A female patient 46 years old: 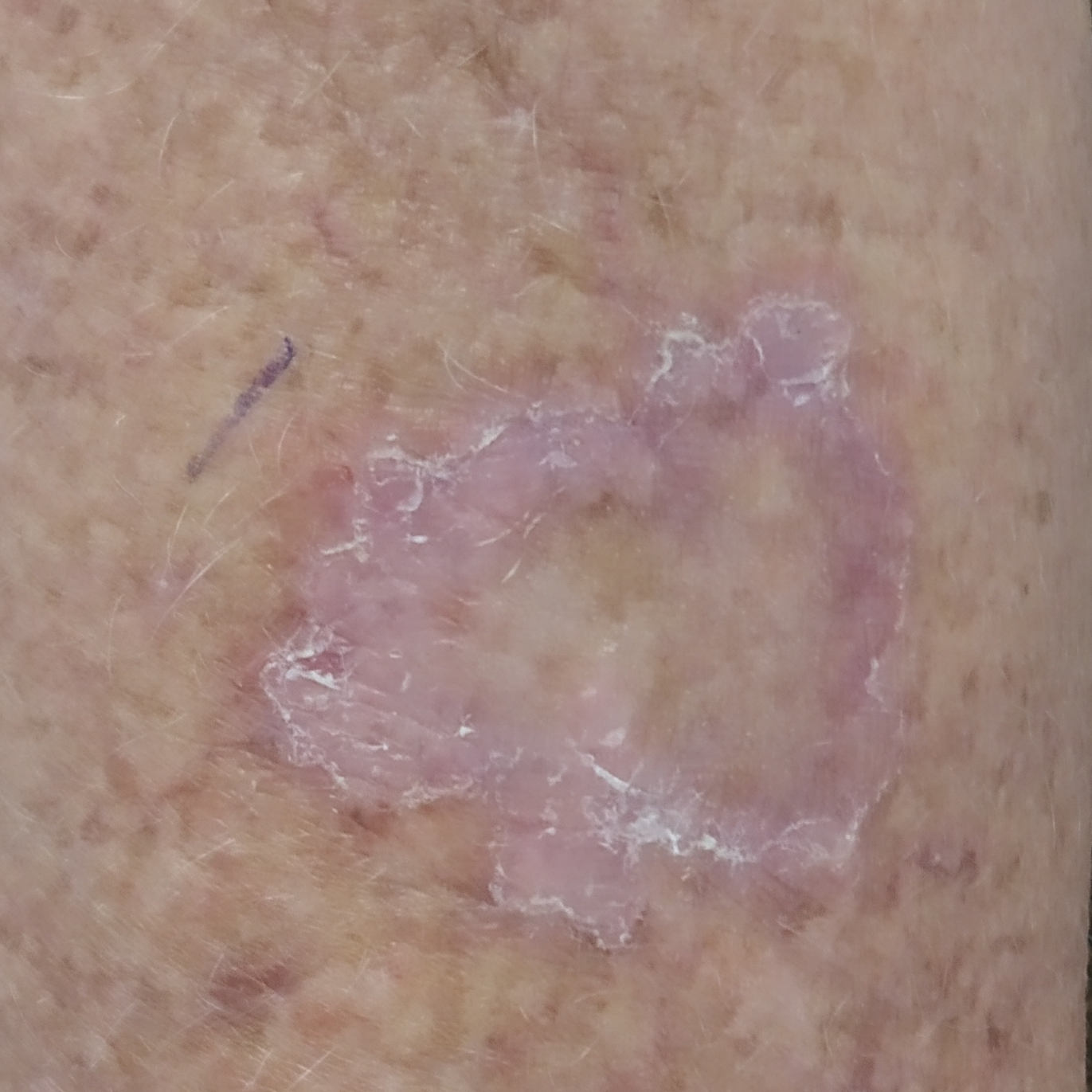anatomic site: a forearm | reported symptoms: itching | pathology: actinic keratosis (biopsy-proven).